The photograph was taken at an angle, located on the arm: 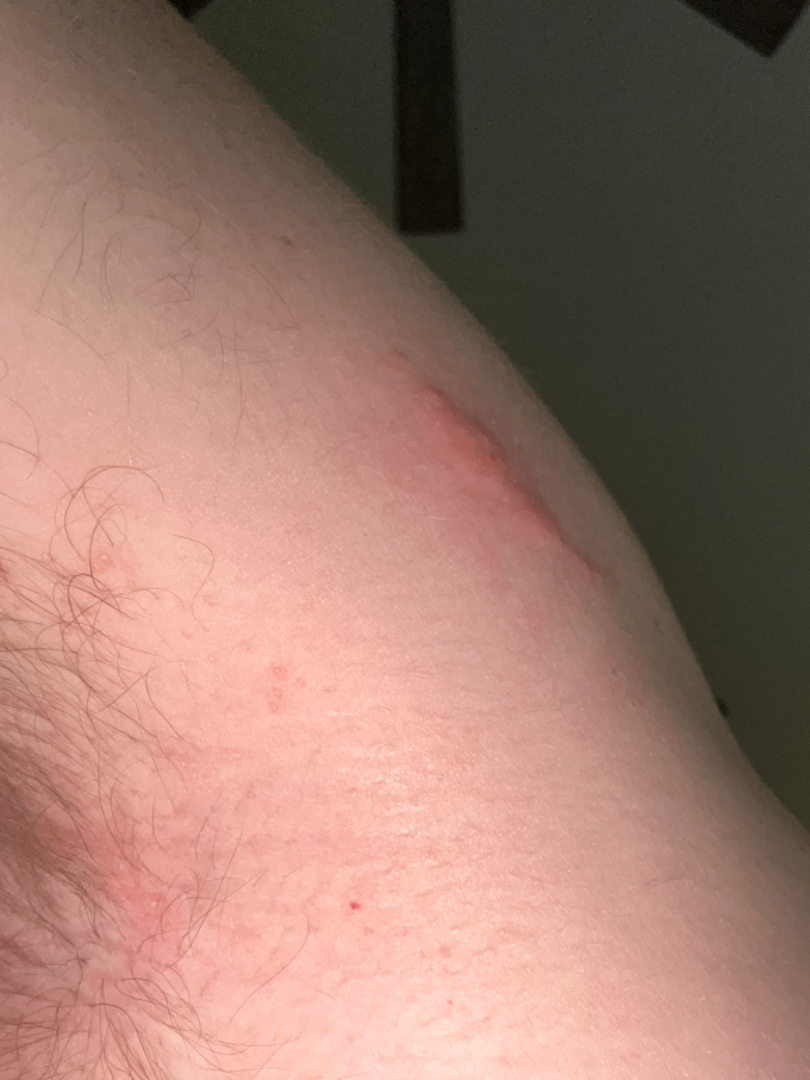No differential diagnosis could be assigned on photographic review.
The contributor reports bothersome appearance and itching.
The condition has been present for about one day.
The patient considered this a rash.
No constitutional symptoms were reported.
Texture is reported as raised or bumpy.